Dermoscopy of a skin lesion.
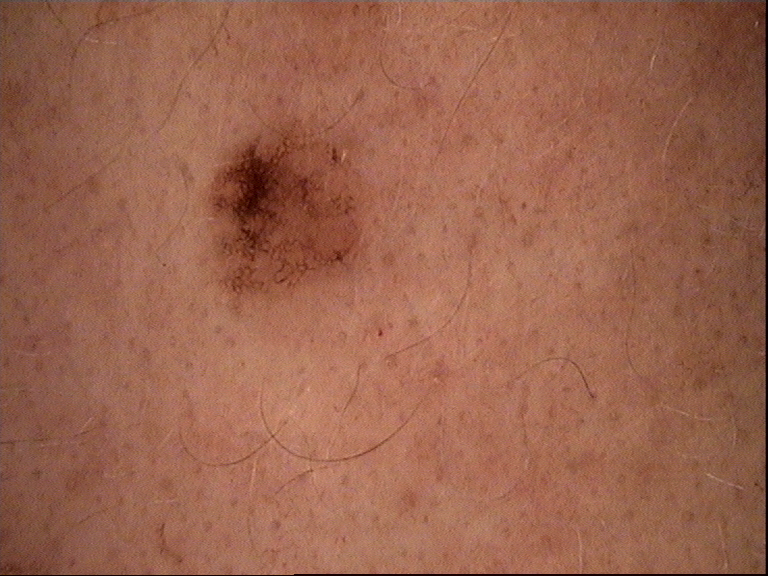The diagnosis was a benign lesion — a dysplastic junctional nevus.